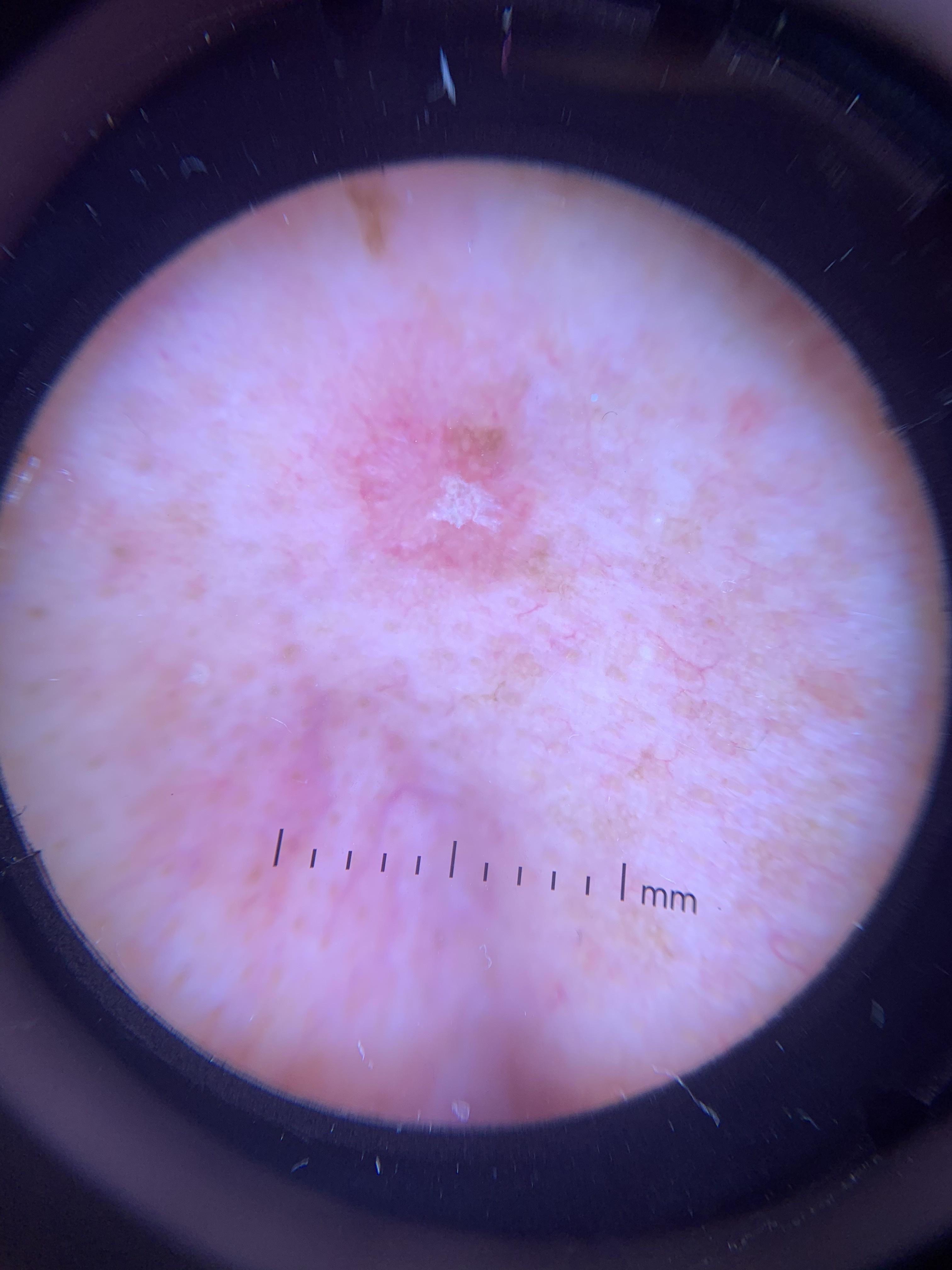Q: What is the diagnosis?
A: Solar or actinic keratosis (biopsy-proven)